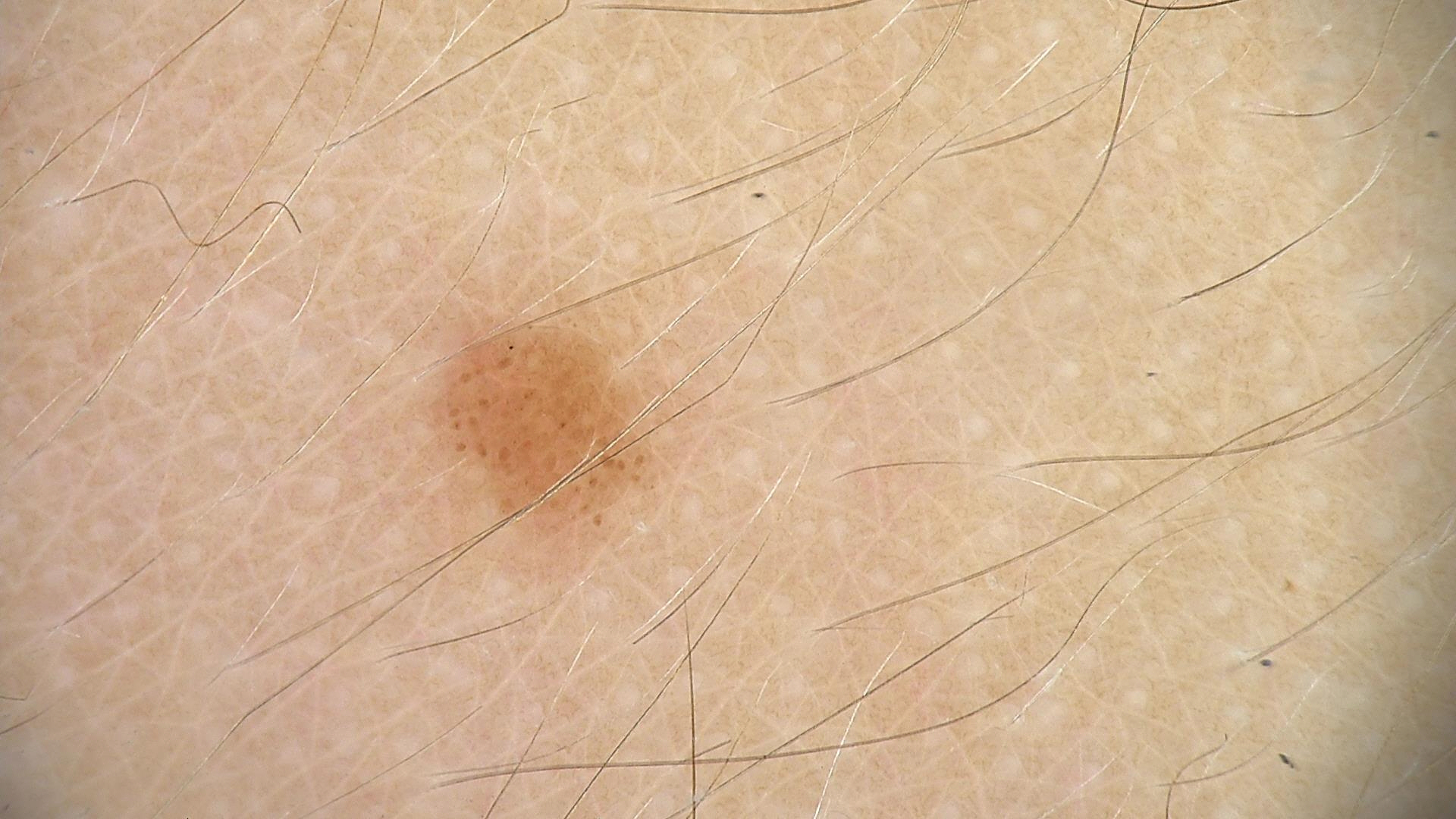A dermatoscopic image of a skin lesion.
Consistent with a dysplastic junctional nevus.